A dermoscopic photograph of a skin lesion: 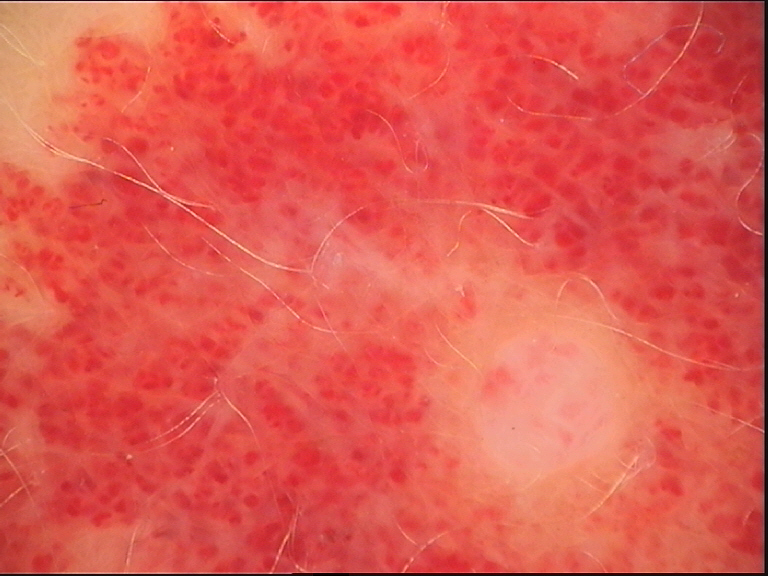This is a vascular lesion.
The diagnostic label was a hemangioma.